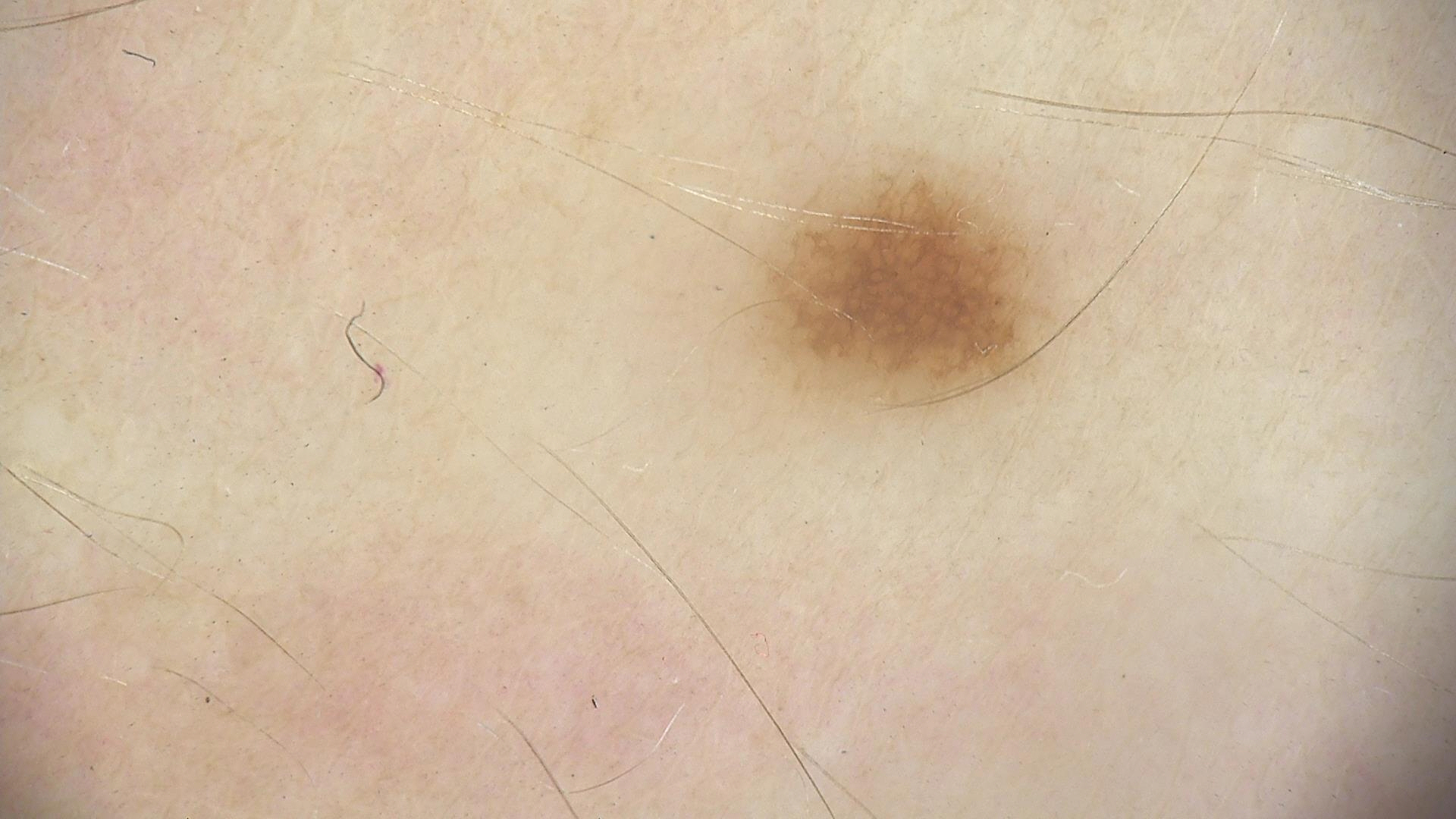Conclusion: The diagnosis was a dysplastic junctional nevus.